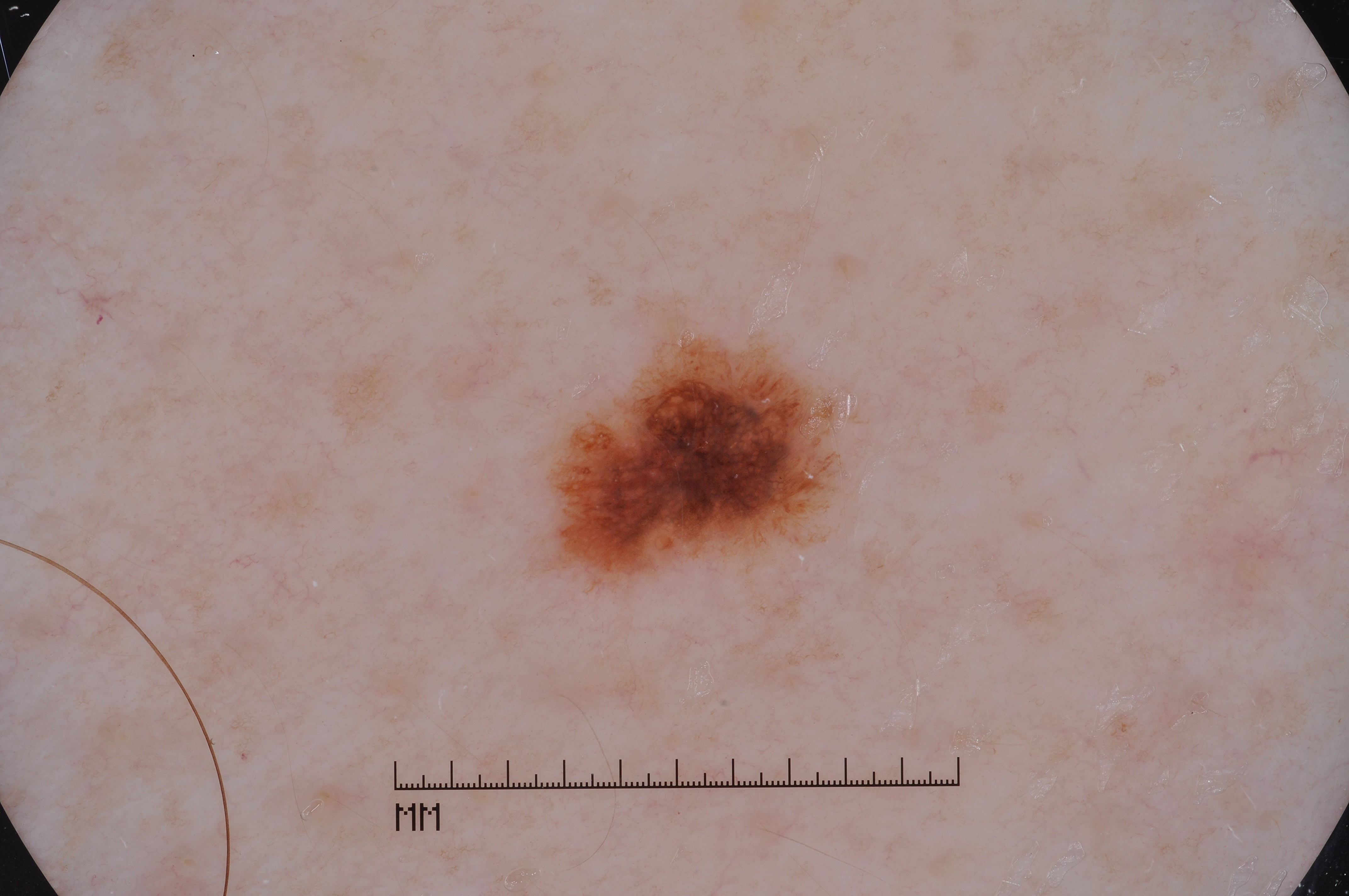image type = dermatoscopic image of a skin lesion; subject = male, aged 63 to 67; lesion extent = small; dermoscopic findings = pigment network and milia-like cysts; bounding box = <box>559, 337, 832, 574</box>; diagnostic label = a melanocytic nevus, a benign lesion.